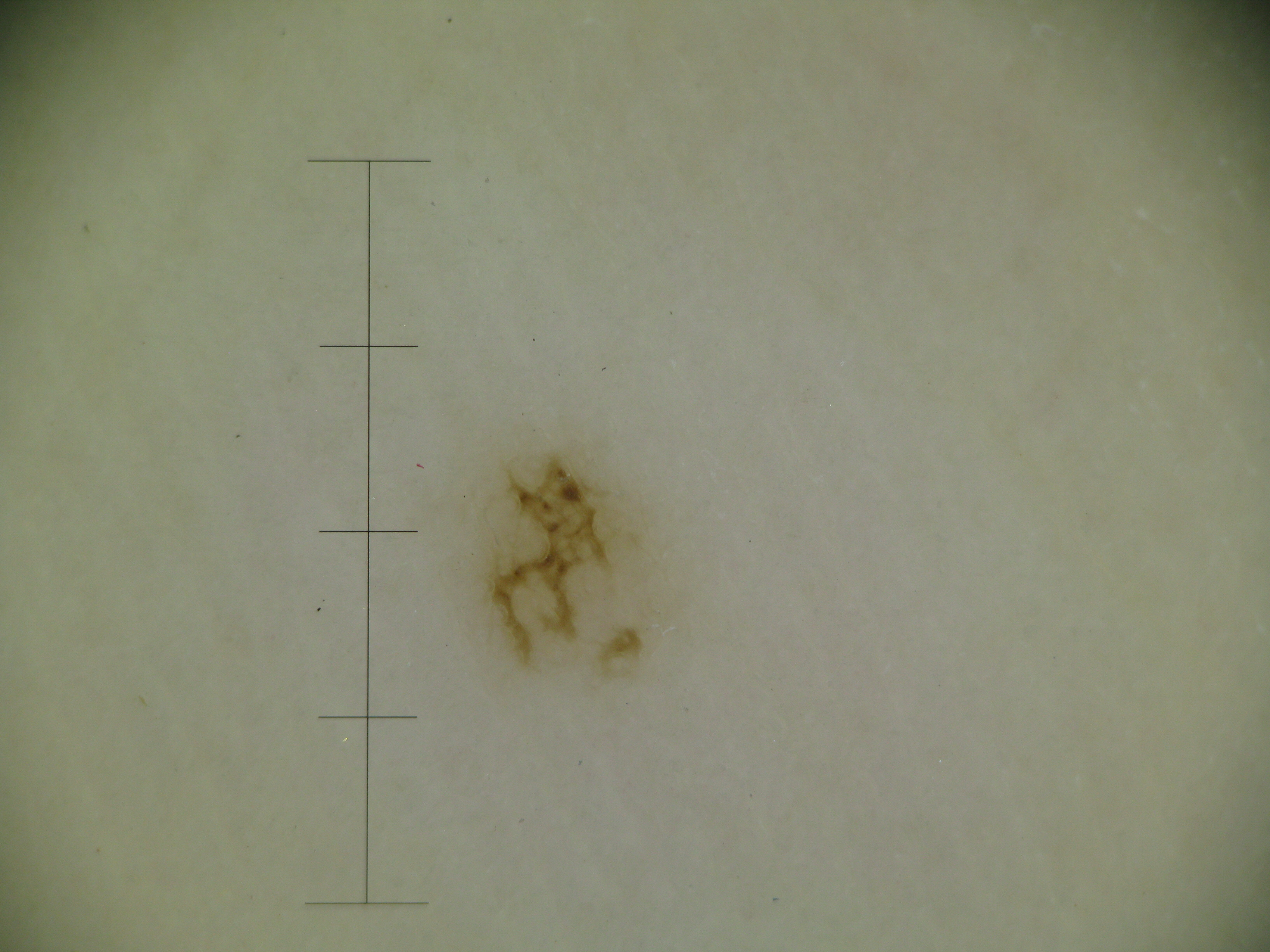Case:
– modality: dermoscopy
– subtype: banal
– diagnosis: acral junctional nevus (expert consensus)